The affected area is the head or neck and arm; a close-up photograph — 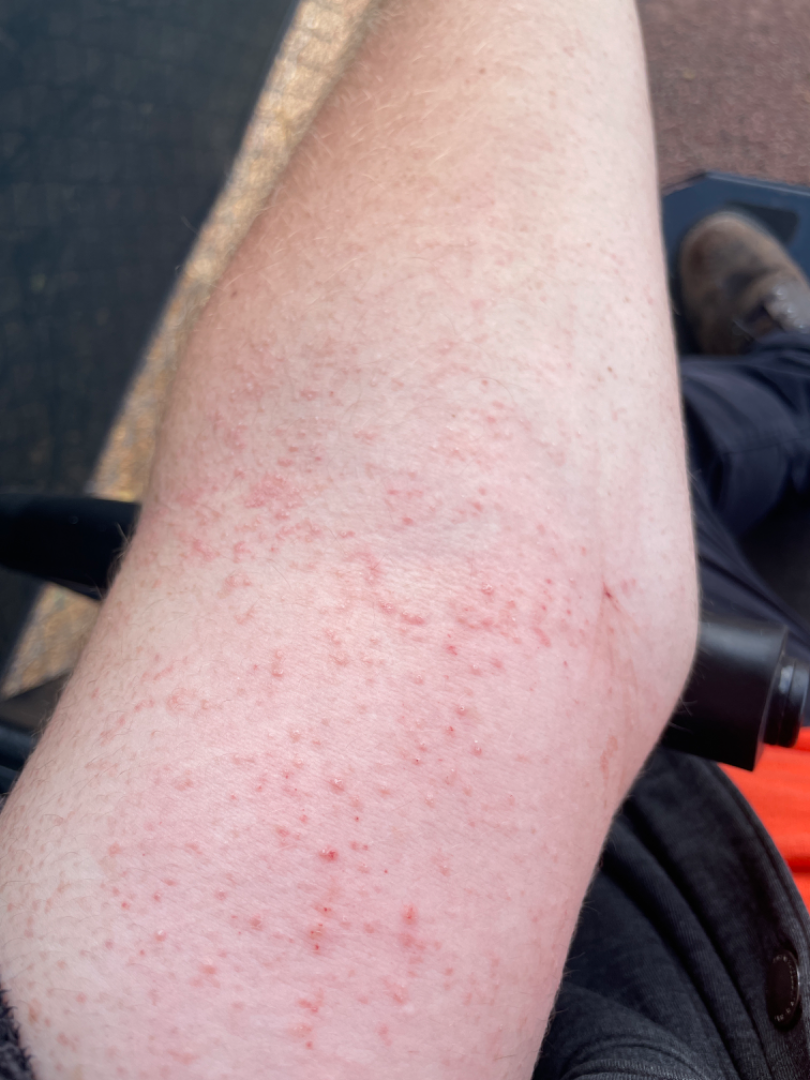On dermatologist assessment of the image, Keratosis pilaris (0.41); Eczema (0.41); Folliculitis (0.18).